Male contributor, age 18–29 · the arm is involved · a close-up photograph — 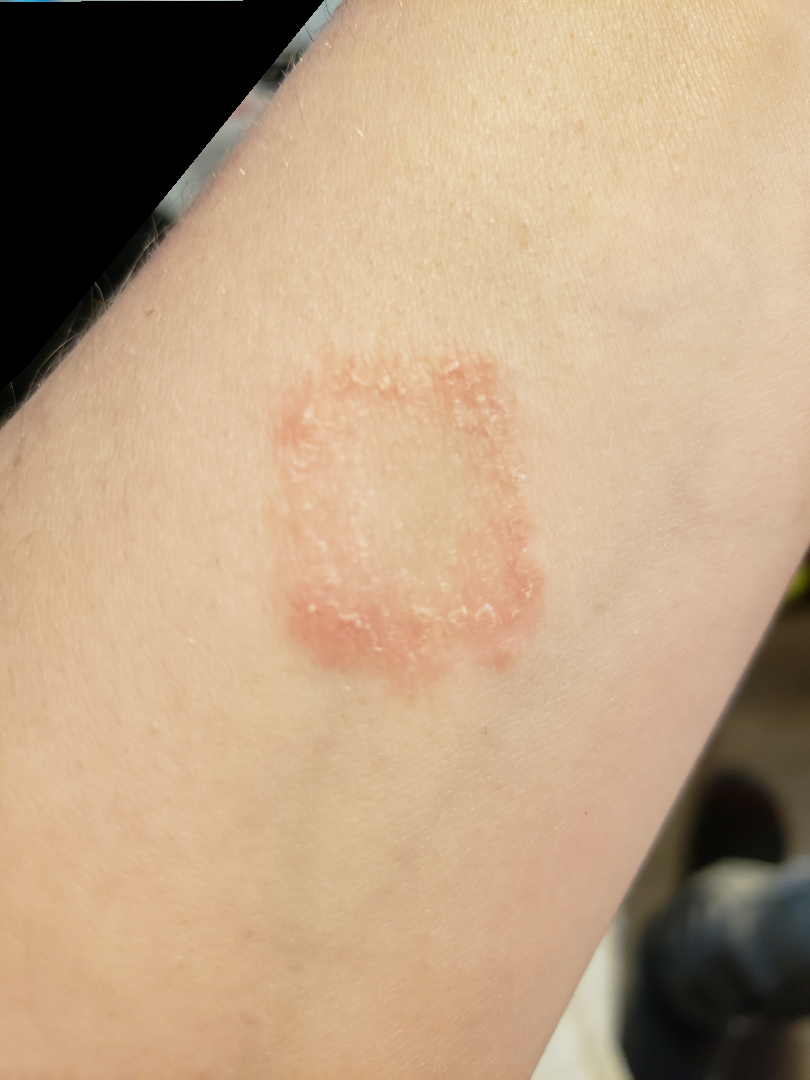other reported symptoms = none reported, self-categorized as = a rash, described texture = rough or flaky, symptoms = bothersome appearance and enlargement, present for = one to four weeks, diagnostic considerations = the differential is split between Eczema and Tinea.